The lesion is associated with itching and bothersome appearance · reported duration is less than one week · the lesion is described as flat and raised or bumpy · the lesion involves the front of the torso and arm · the subject is 30–39, male · close-up view.
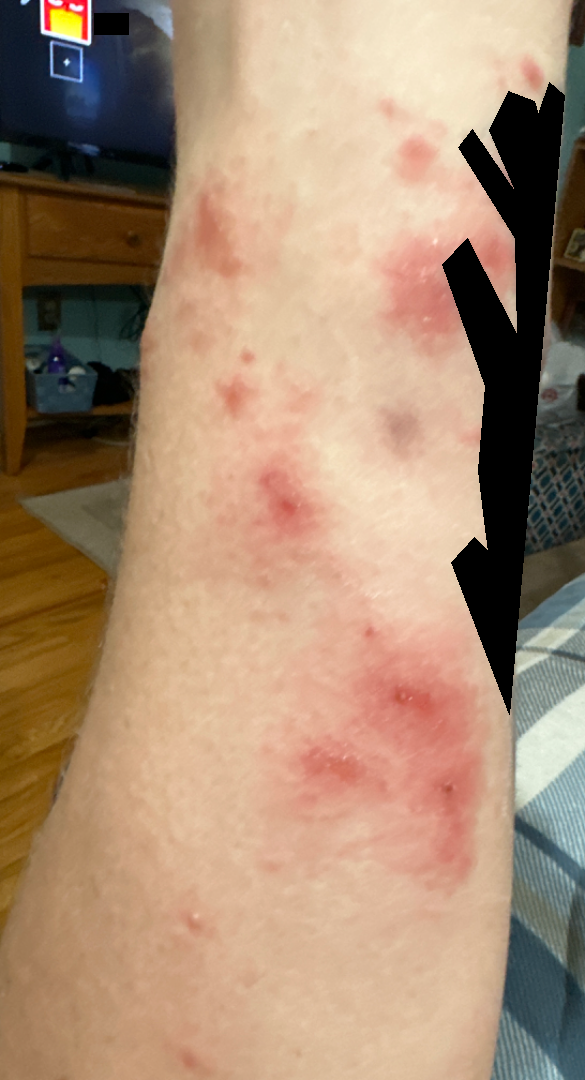Single-reviewer assessment: favoring Allergic Contact Dermatitis; an alternative is Bullous dermatosis; with consideration of Deep fungal infection.